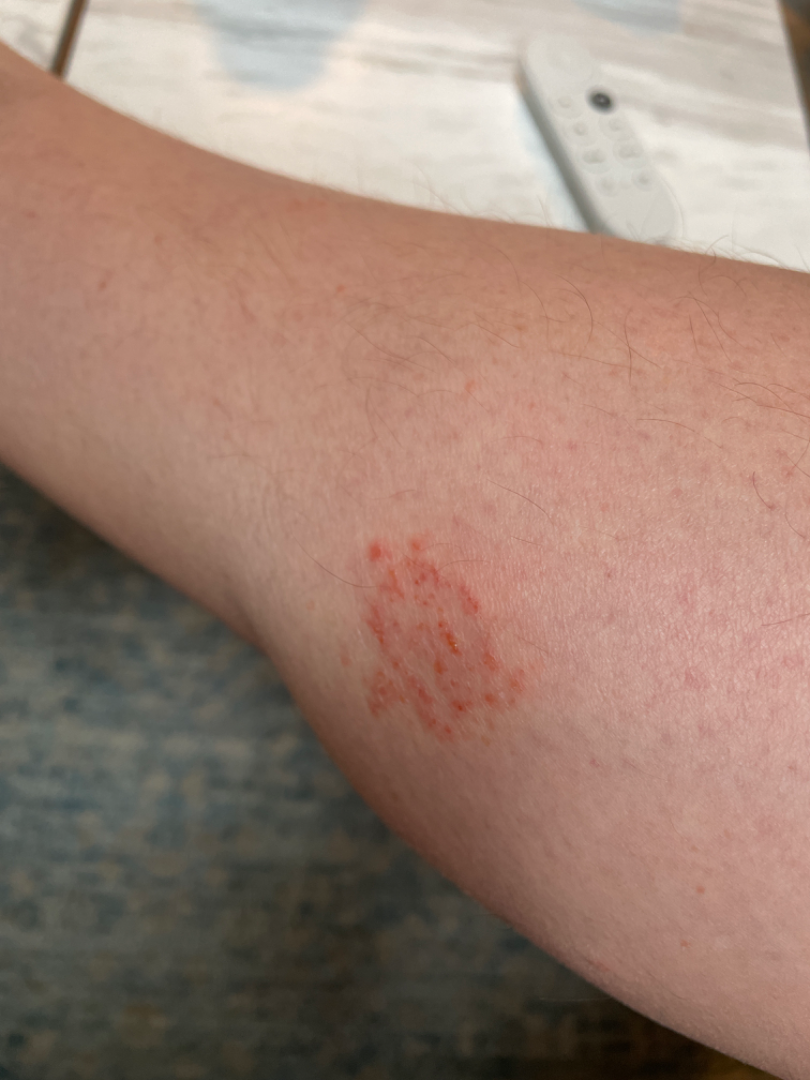The skin findings could not be characterized from the image. The patient described the issue as a rash. The patient indicates the condition has been present for one to four weeks. The subject is a male aged 40–49. The photograph was taken at an angle. The lesion is described as raised or bumpy. The lesion is associated with bothersome appearance and itching. The affected area is the leg.